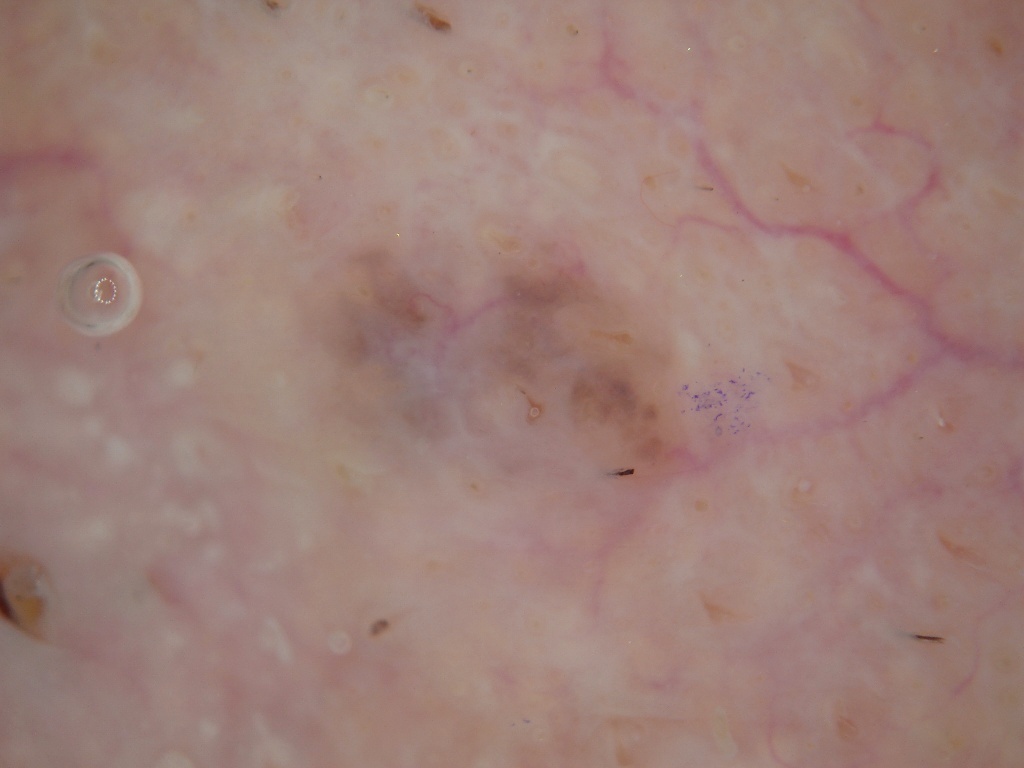  patient:
    sex: male
    age_approx: 65
  image:
    modality: dermoscopy
  dermoscopic_features:
    present: []
    absent:
      - negative network
      - pigment network
      - milia-like cysts
      - globules
      - streaks
  lesion_location:
    bbox_xyxy:
      - 143
      - 103
      - 858
      - 757
  diagnosis:
    name: melanocytic nevus
    malignancy: benign
    lineage: melanocytic
    provenance: clinical